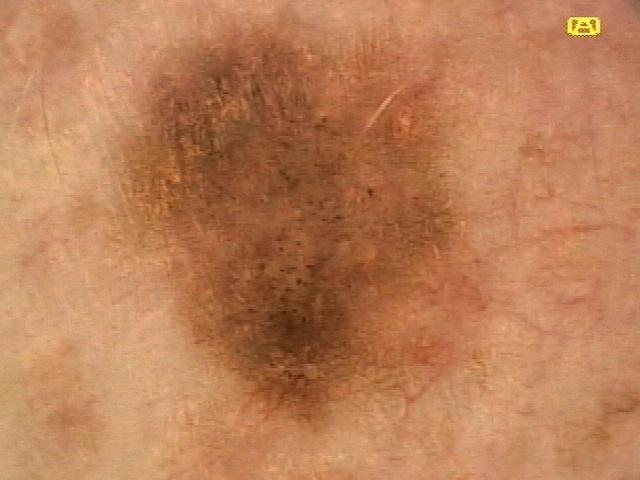Q: Patient demographics?
A: male, in their 40s
Q: What is the anatomic site?
A: the trunk
Q: What did the workup show?
A: Nevus (biopsy-proven)